A dermoscopic image of a skin lesion: 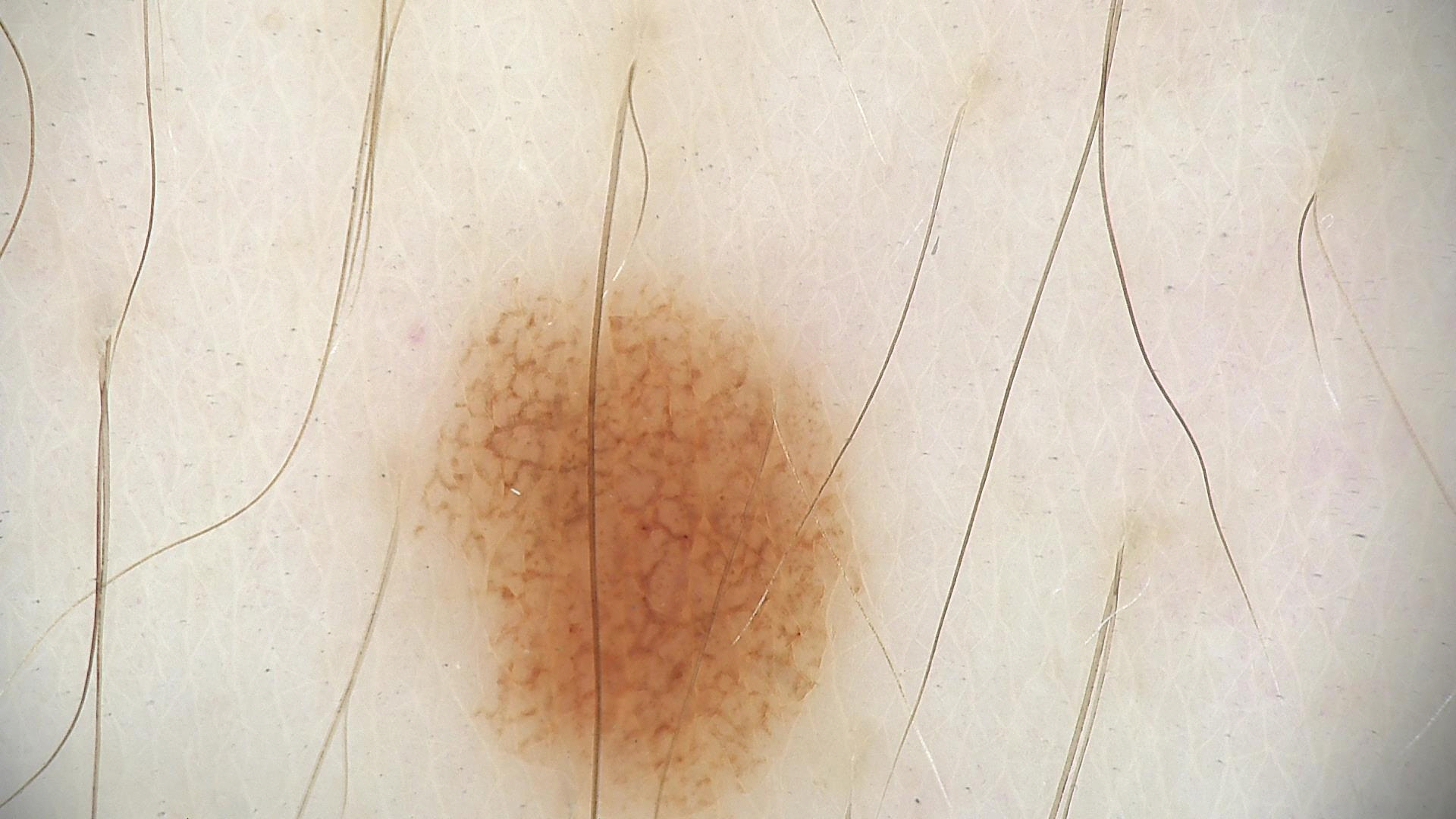Consistent with a dysplastic junctional nevus.